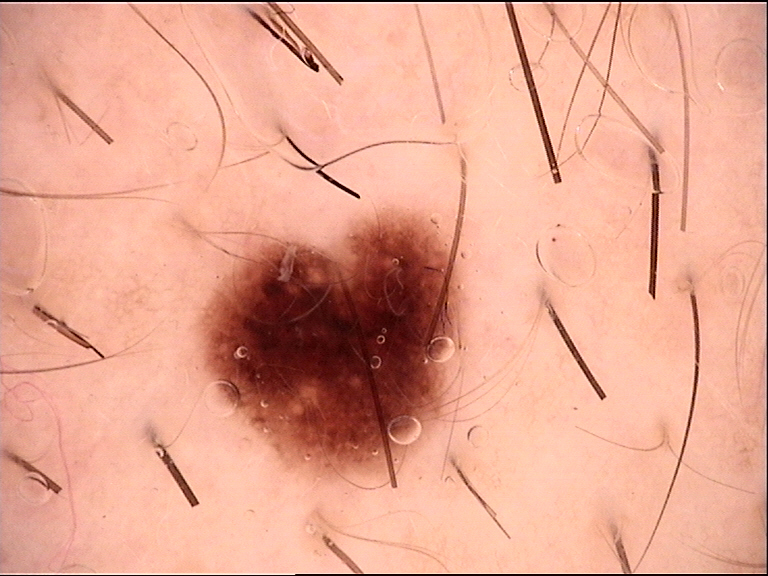modality = dermatoscopy; class = dysplastic junctional nevus (expert consensus).